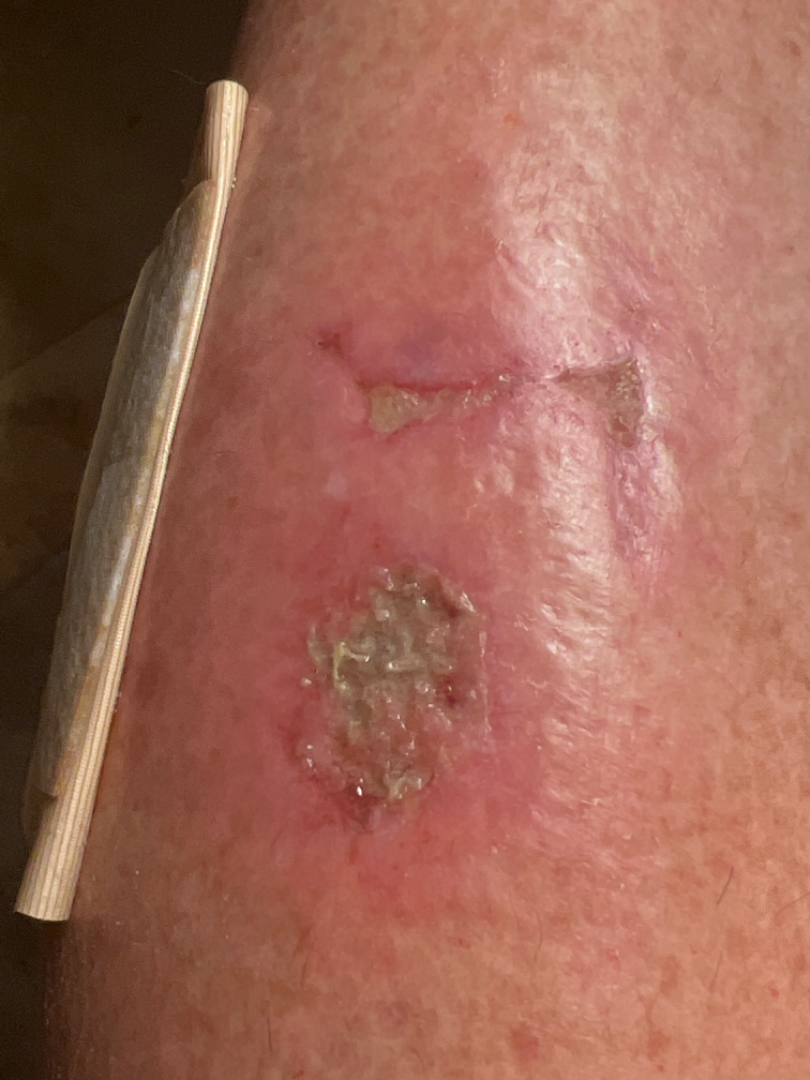| feature | finding |
|---|---|
| assessment | not assessable |